A skin lesion imaged with a dermatoscope · a male subject aged approximately 40.
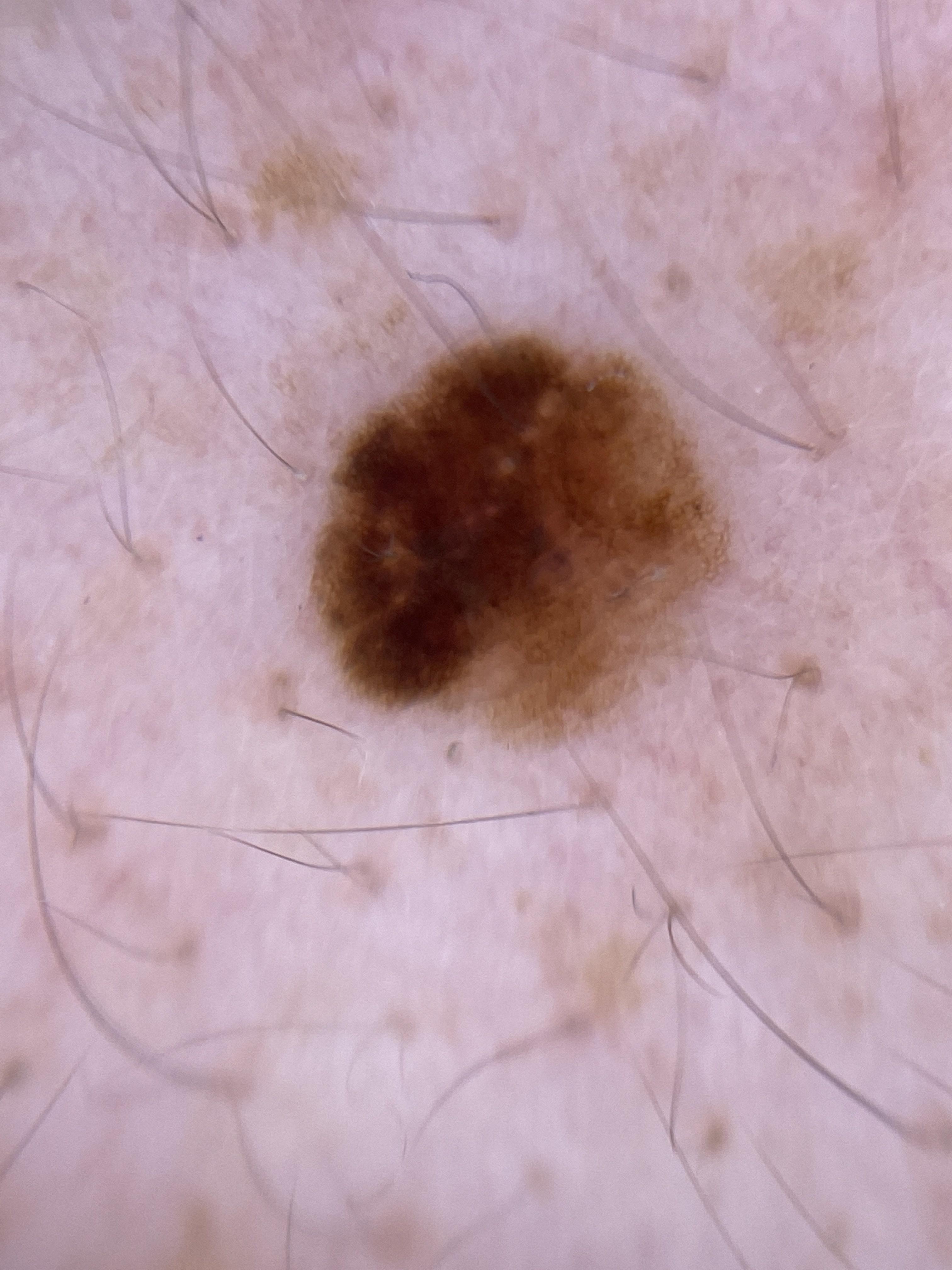Findings:
The lesion is located on the trunk.
Diagnosis:
Histopathologically confirmed as a melanoma.